A dermoscopic close-up of a skin lesion.
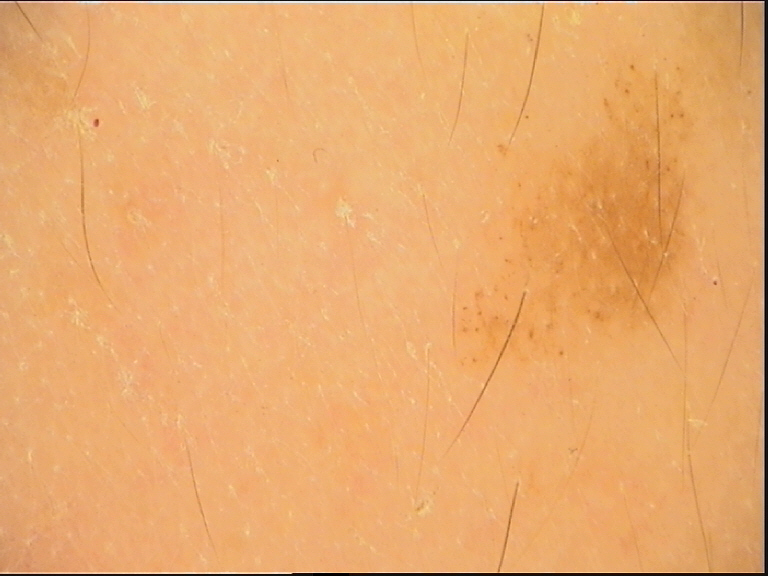Case:
- class · dysplastic junctional nevus (expert consensus)